A skin lesion imaged with a dermatoscope:
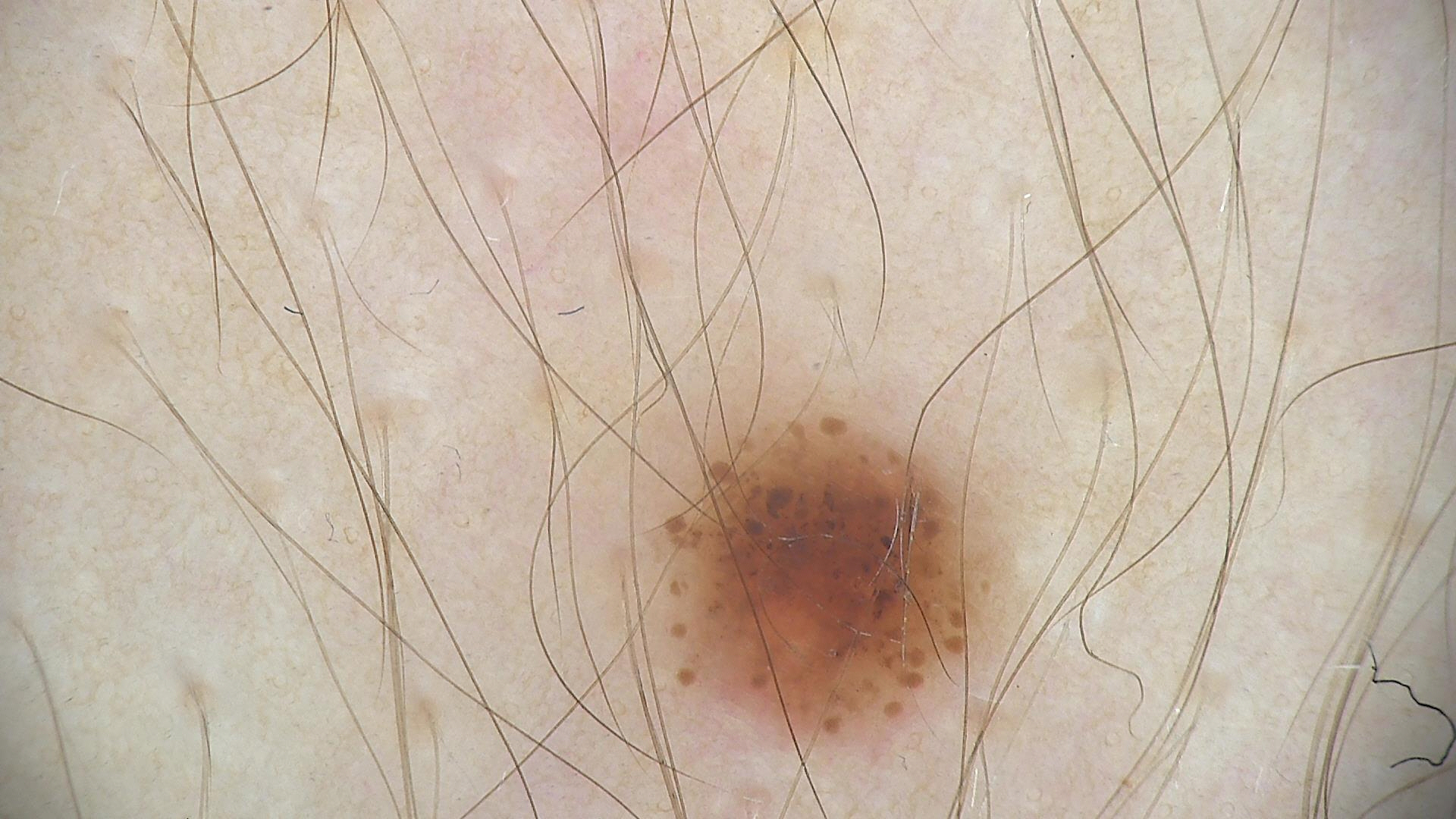The diagnosis was a dysplastic junctional nevus.